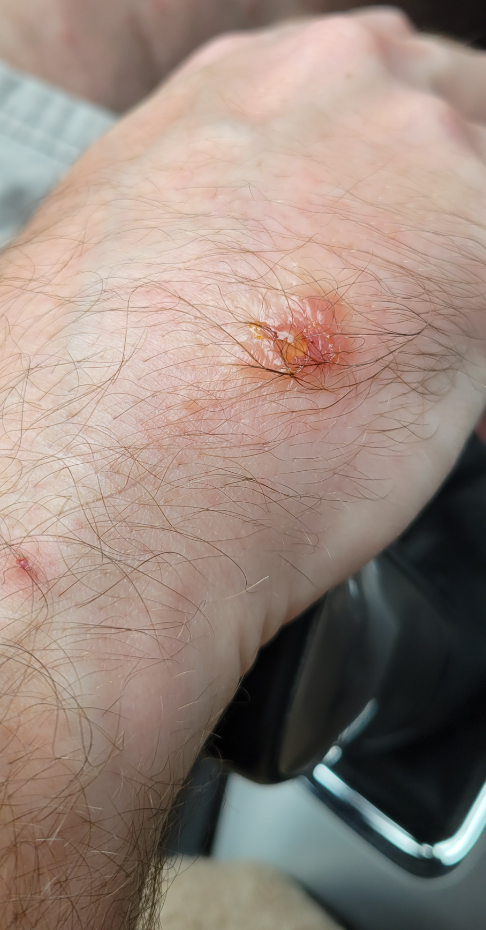– location: back of the torso, leg and arm
– framing: close-up
– differential diagnosis: consistent with Allergic Contact Dermatitis